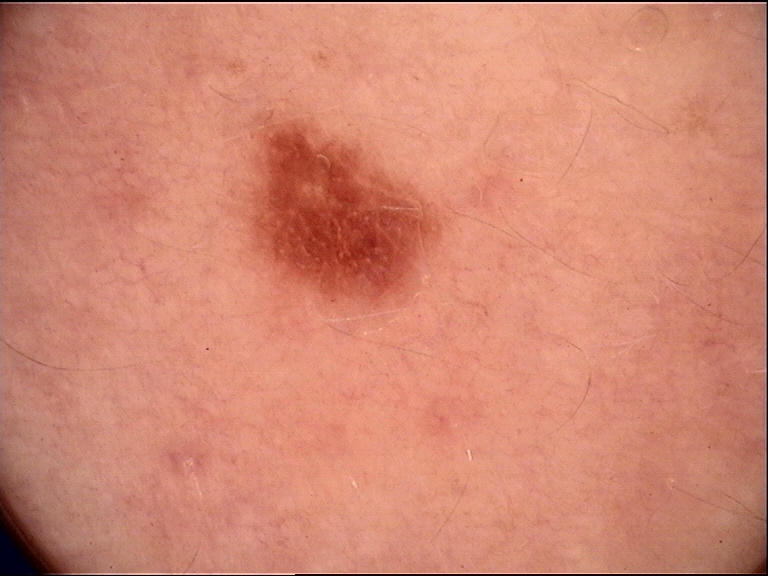Findings:
– assessment — dysplastic junctional nevus (expert consensus)